A female patient aged approximately 65; the chart records a previous melanoma; Fitzpatrick phototype I — 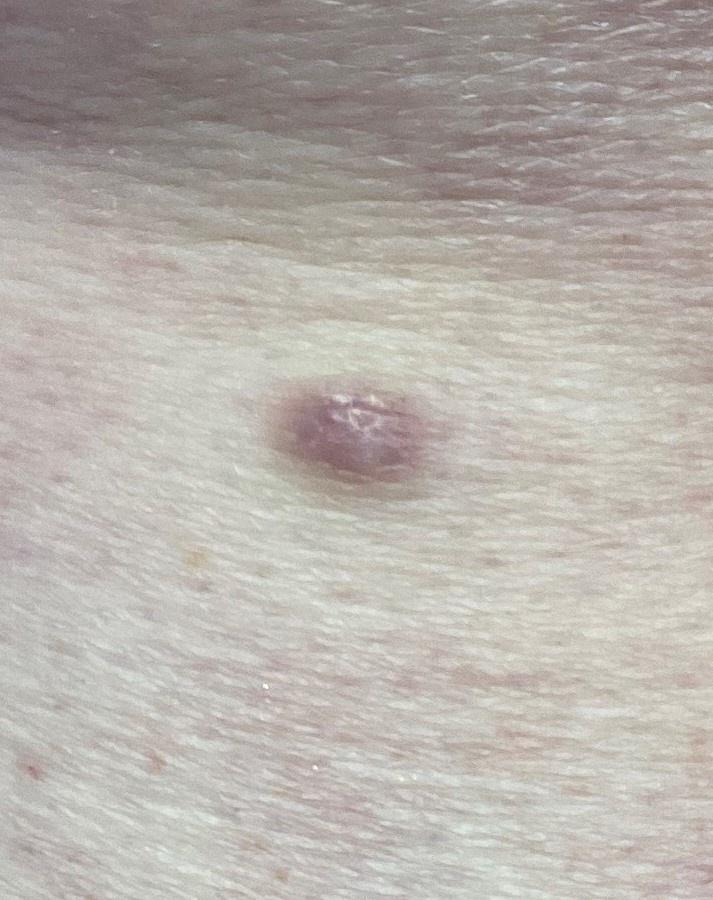Expert review favored a dermatofibroma.